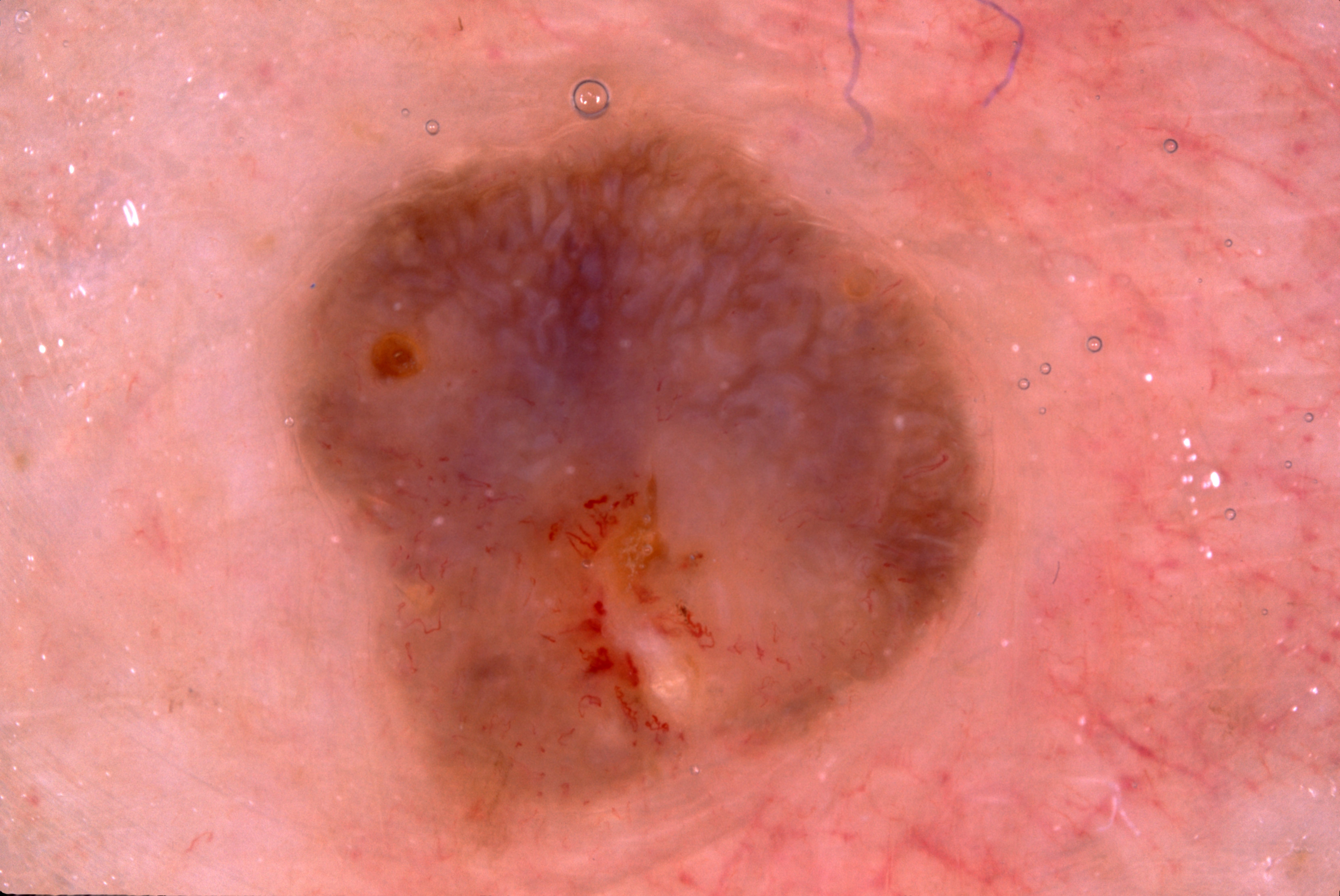subject = female, aged 83 or over
image = dermoscopy of a skin lesion
dermoscopic features = milia-like cysts; absent: pigment network, negative network, and streaks
lesion bbox = [283, 105, 1005, 868]
lesion extent = large
assessment = a seborrheic keratosis, a non-melanocytic (keratinocytic) lesion